A skin lesion imaged with a dermatoscope.
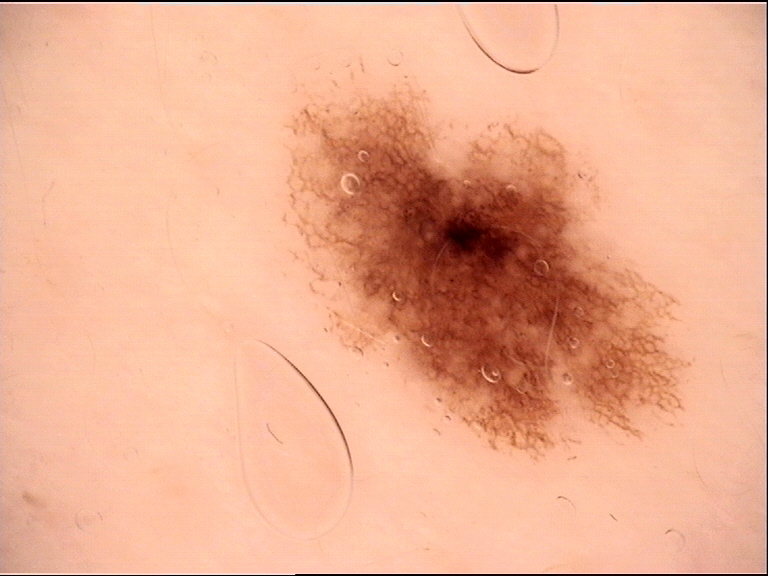Diagnosed as a benign lesion — a dysplastic junctional nevus.